The photo was captured at a distance. The patient is a female aged 40–49. The affected area is the sole of the foot:
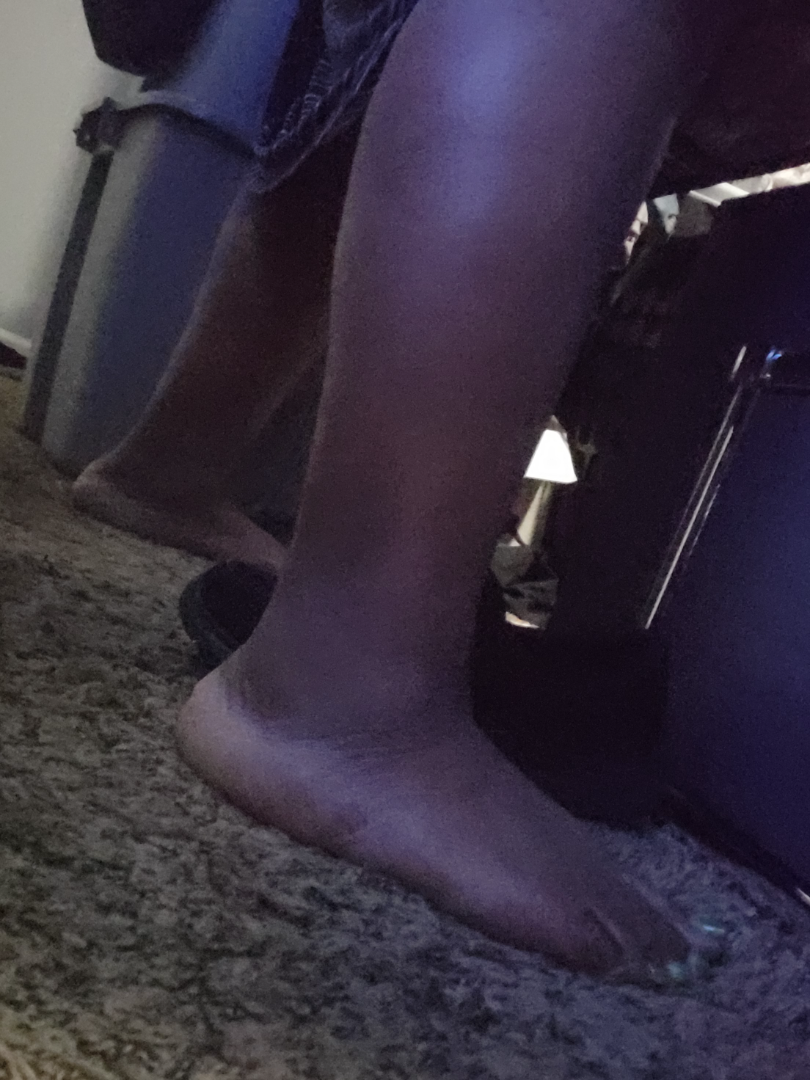Findings:
On photographic review, Tinea and Eczema were considered with similar weight; less probable is Psoriasis.